A dermoscopic image of a skin lesion.
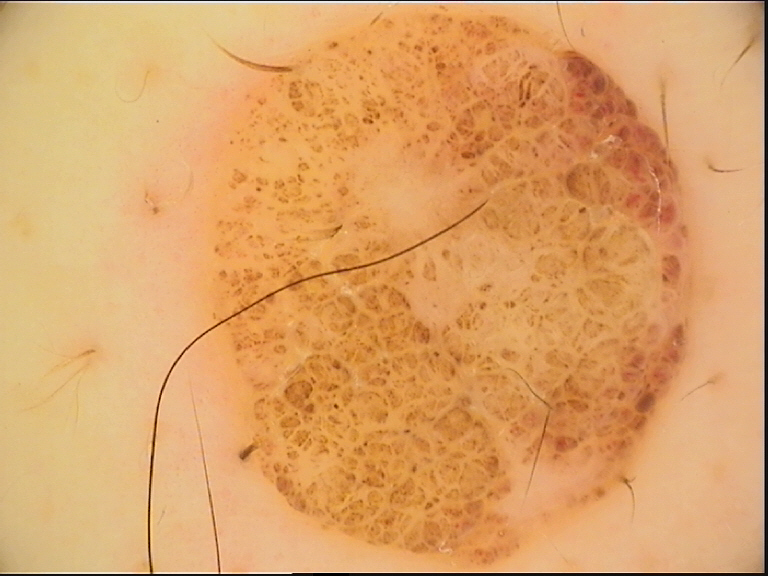The architecture is that of a banal lesion.
Classified as a compound nevus.